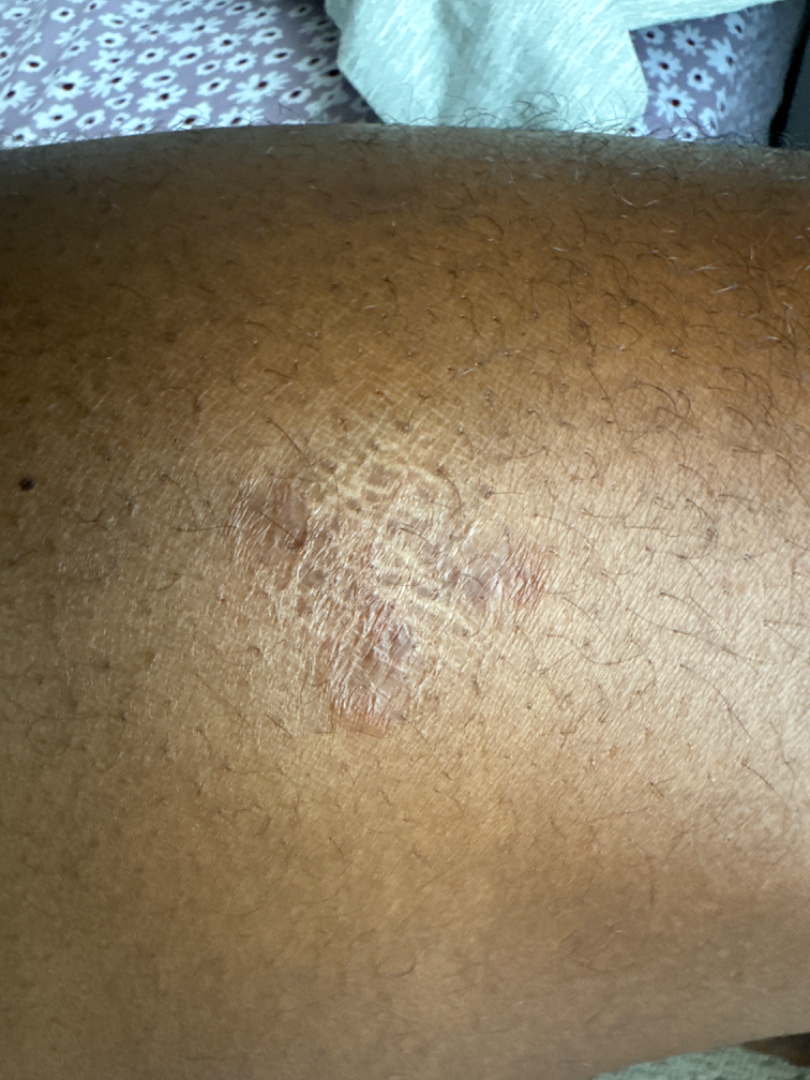{
  "symptoms": "itching",
  "patient_category": "a rash",
  "skin_tone": {
    "fitzpatrick": "VI",
    "monk_skin_tone": [
      5,
      7
    ]
  },
  "duration": "one to four weeks",
  "shot_type": "close-up",
  "body_site": "leg",
  "patient": "male, age 18–29",
  "differential": {
    "leading": [
      "Chronic dermatitis, NOS"
    ],
    "considered": [
      "Irritant Contact Dermatitis"
    ]
  }
}